A skin lesion imaged with a dermatoscope: 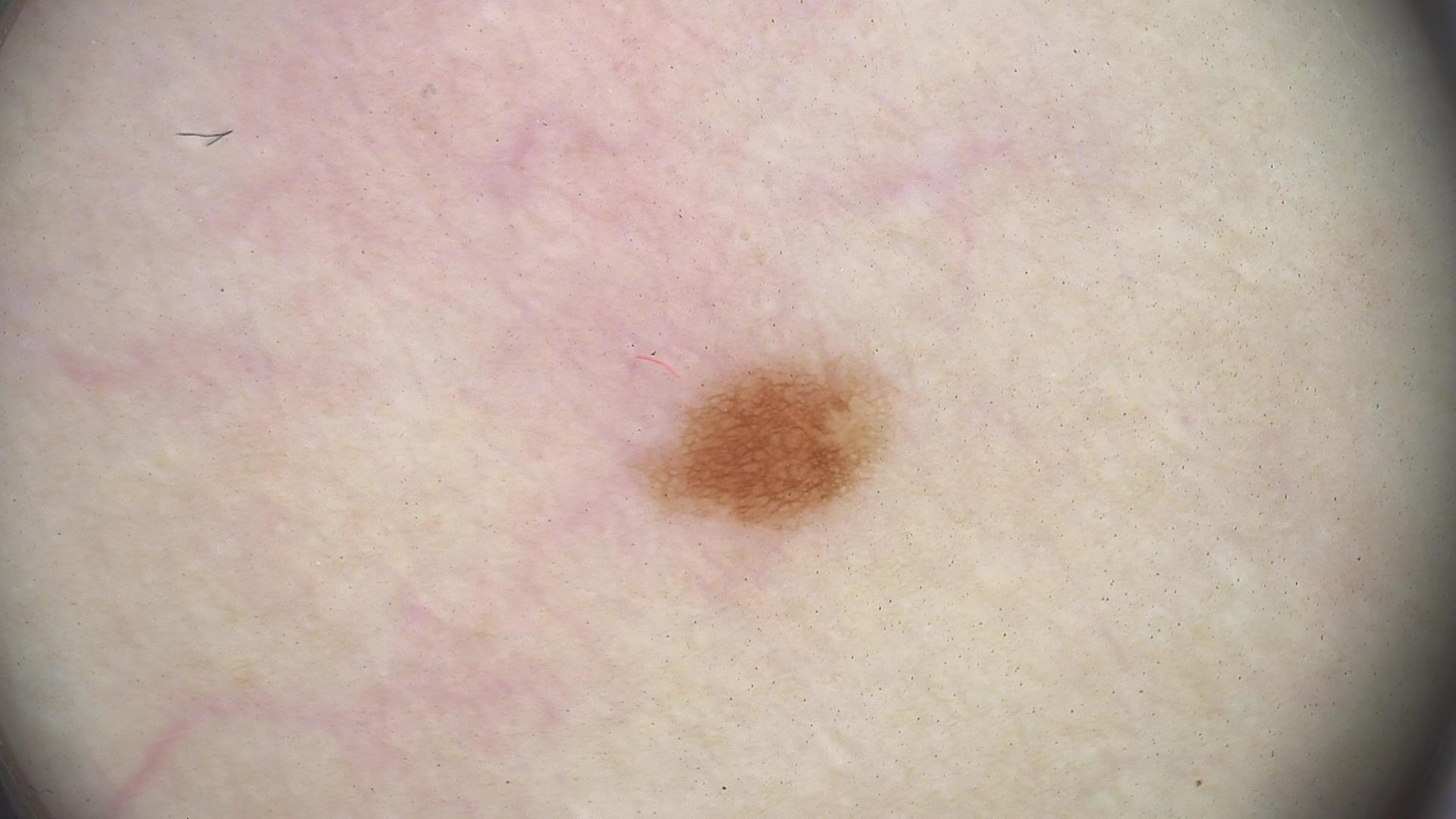Summary: This is a banal lesion. Impression: Consistent with a junctional nevus.